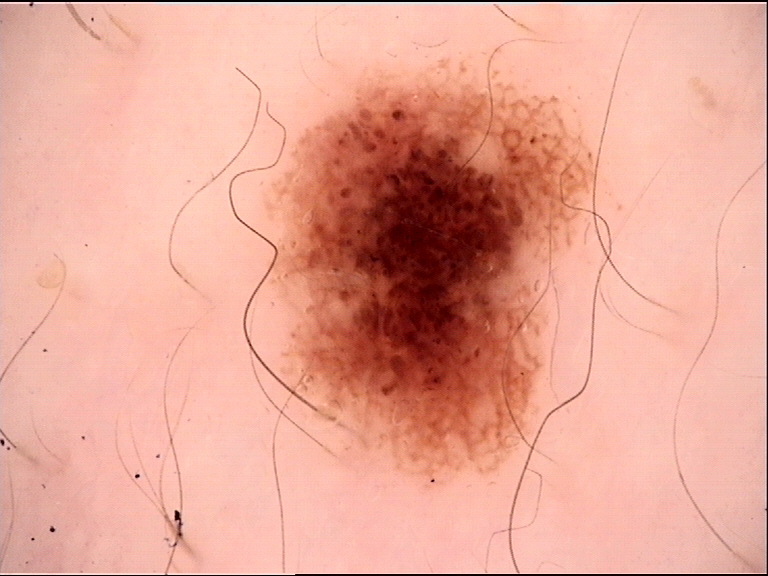A dermoscopy image of a single skin lesion. Classified as a dysplastic junctional nevus.